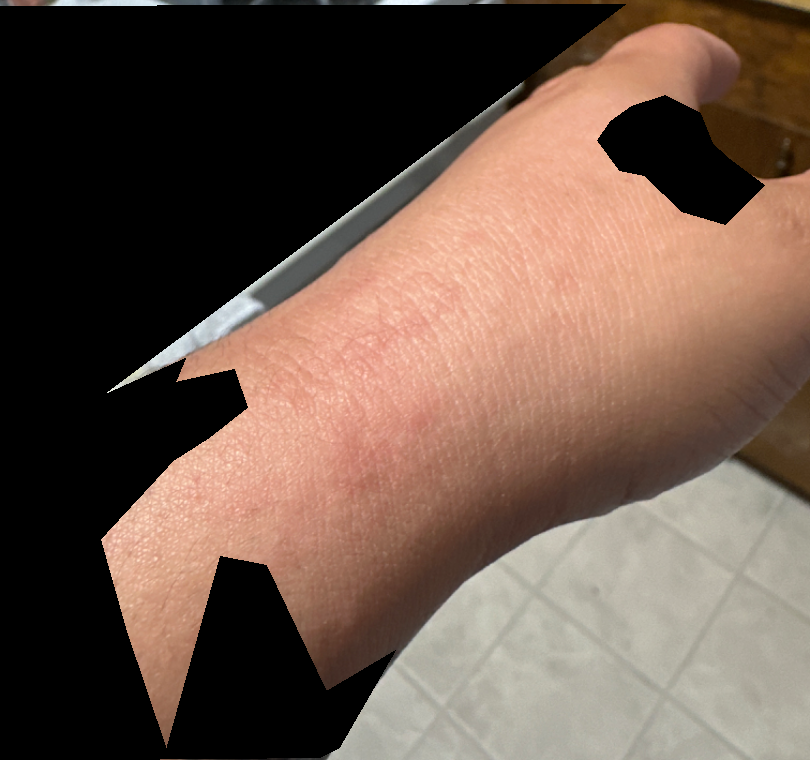Patient information:
The patient reports the condition has been present for one to four weeks. The photo was captured at an angle. The arm and back of the hand are involved. The lesion is described as raised or bumpy. The patient is 18–29, female. Reported lesion symptoms include itching. Skin tone: Fitzpatrick phototype IV; lay graders estimated Monk Skin Tone 2 or 4. The patient described the issue as a rash.
Review:
On independent review by the dermatologists, the impression was split between Contact dermatitis and Allergic Contact Dermatitis; lower on the differential is Urticaria; less probable is Hypersensitivity.